A dermoscopic photograph of a skin lesion:
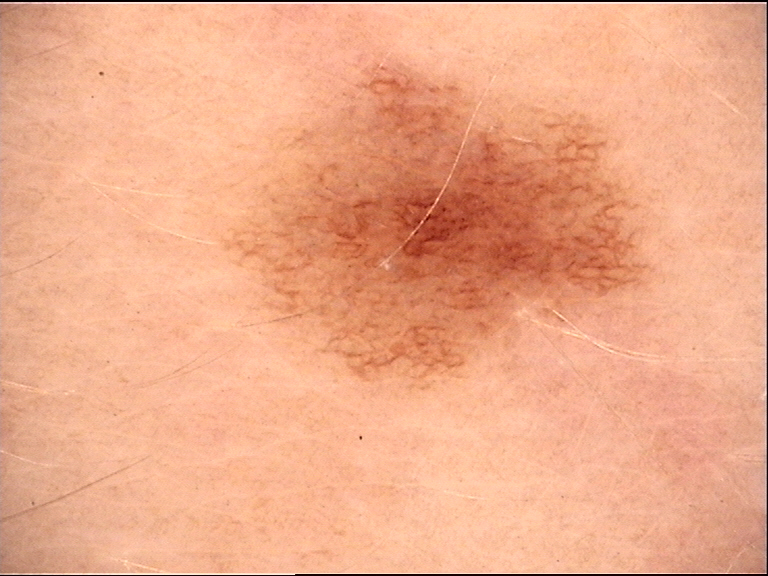Case:
The architecture is that of a banal lesion.
Conclusion:
Consistent with a junctional nevus.